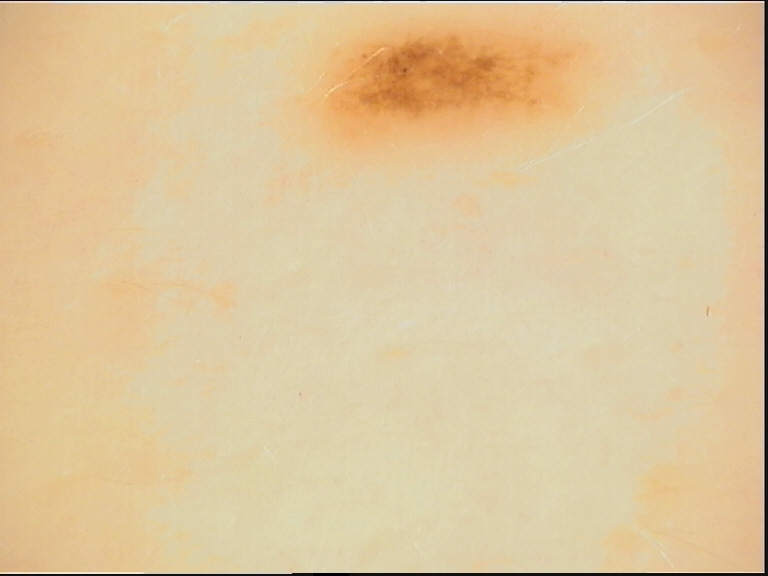Classified as a dysplastic junctional nevus.